This image was taken at a distance · symptoms reported: itching · the affected area is the leg · male patient, age 18–29 · the patient described the issue as a rash · texture is reported as raised or bumpy · skin tone: FST III · present for about one day:
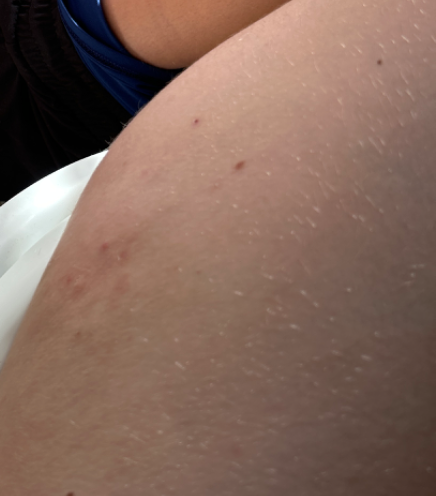Diagnostic features were not clearly distinguishable in this photograph.